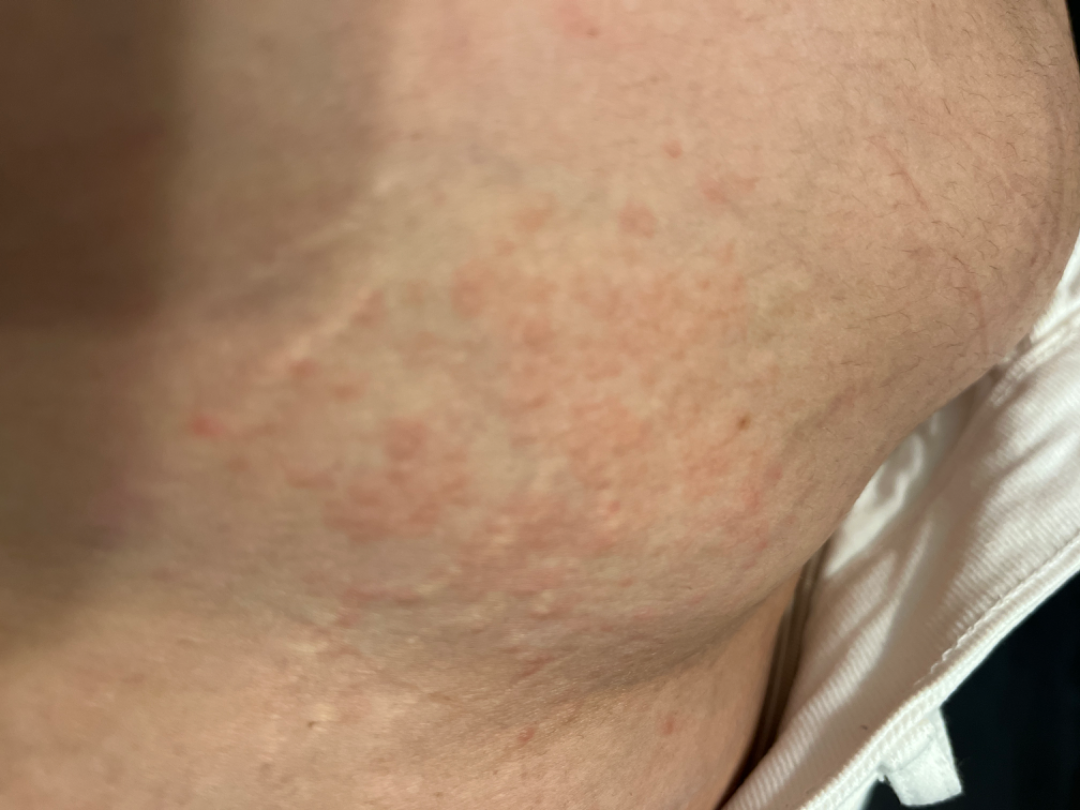Q: Could the case be diagnosed?
A: indeterminate from the photograph
Q: Duration?
A: less than one week
Q: Who is the patient?
A: female
Q: Anatomic location?
A: front of the torso
Q: Texture?
A: raised or bumpy
Q: How was the photo taken?
A: close-up